A dermoscopy image of a single skin lesion.
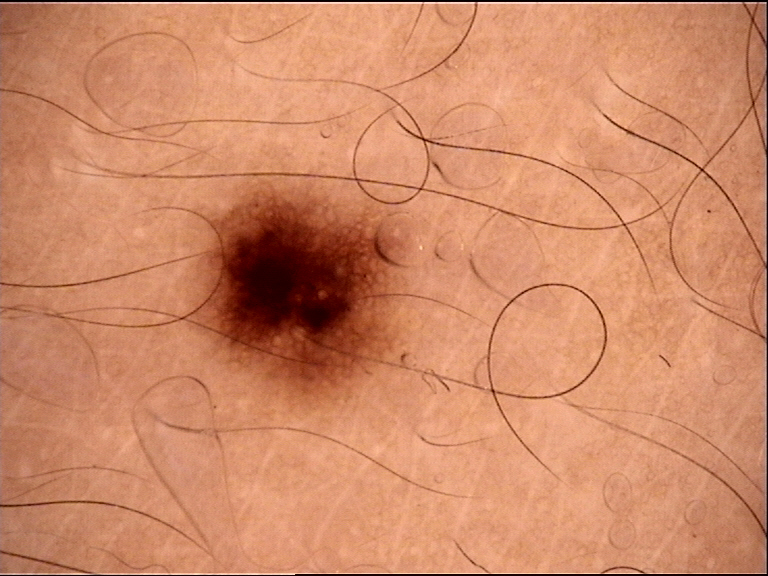diagnosis:
  name: junctional nevus
  code: jb
  malignancy: benign
  super_class: melanocytic
  confirmation: expert consensus